A female subject in their 30s:
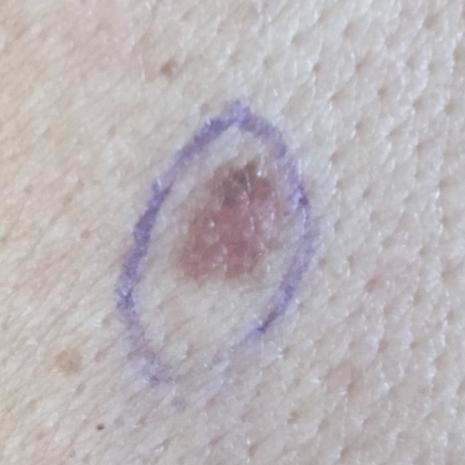Located on the back. No symptoms reported. Clinically diagnosed as a nevus.